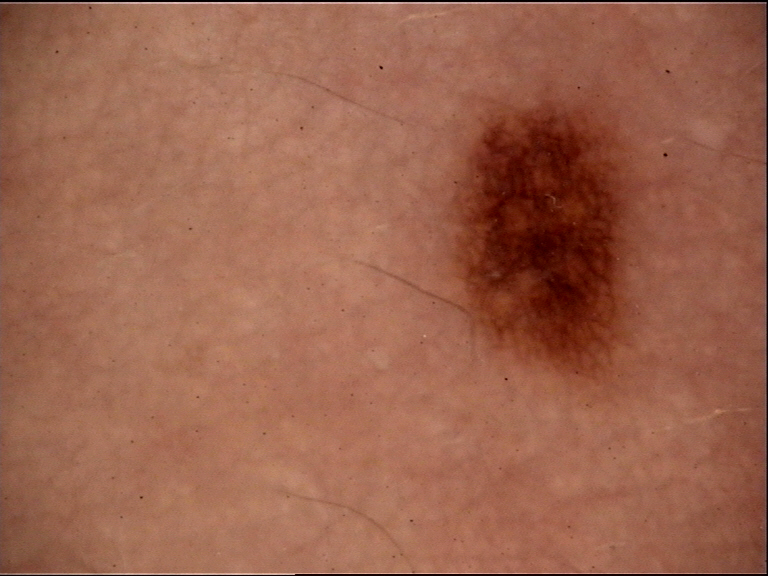class: dysplastic junctional nevus (expert consensus).